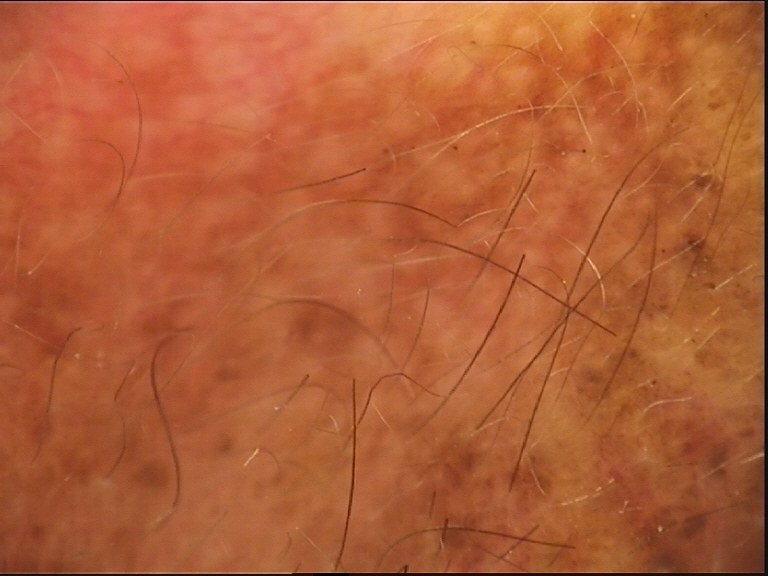- modality · dermoscopy
- diagnostic label · congenital compound nevus (expert consensus)